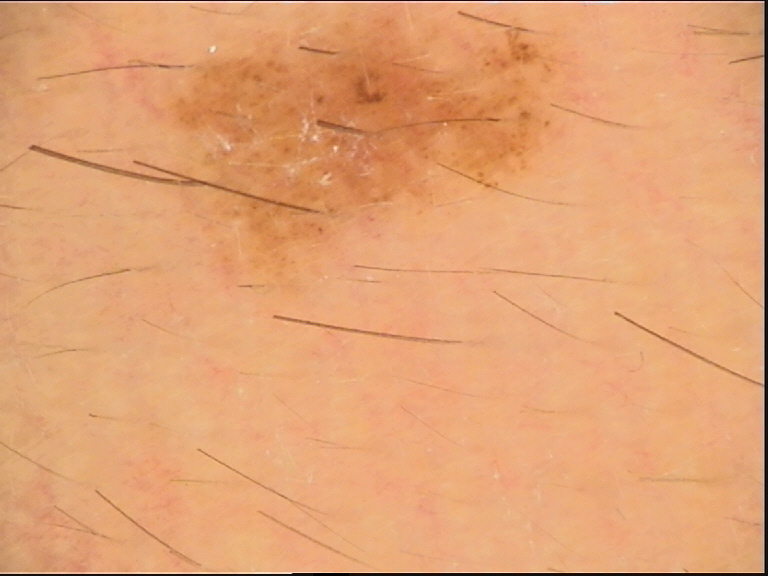Impression:
Labeled as a dysplastic junctional nevus.